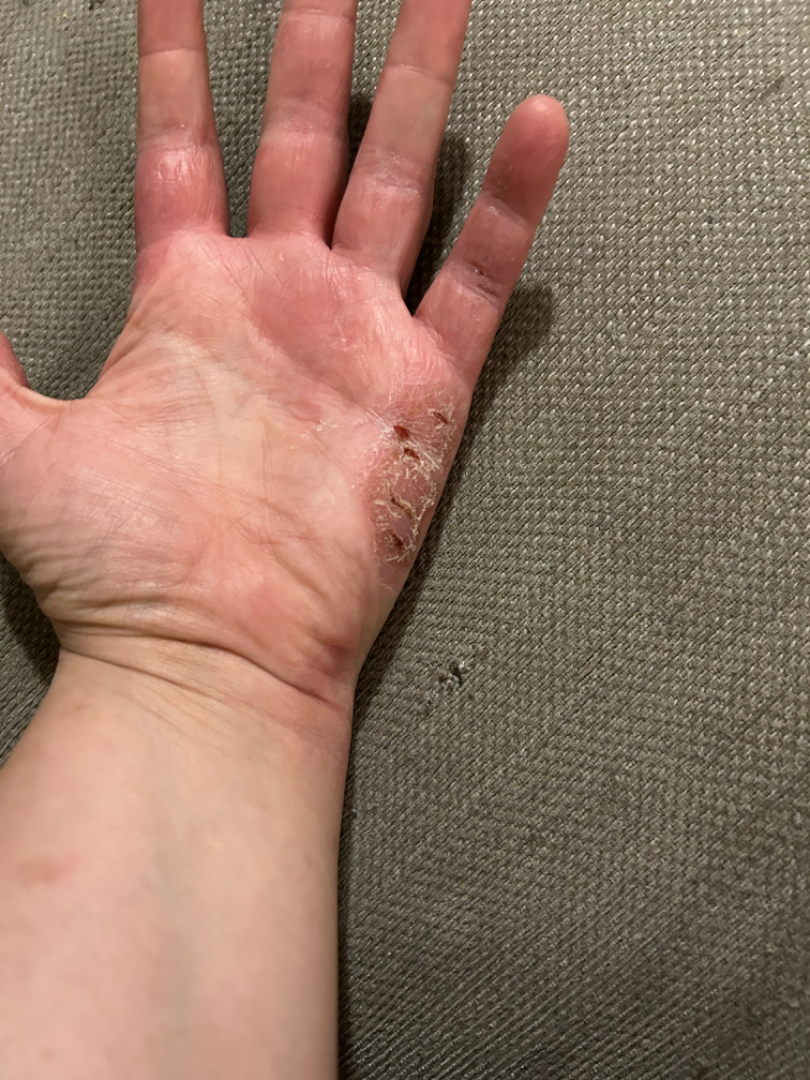An image taken at an angle.
Present for more than one year.
The patient described the issue as a rash.
The contributor reports bleeding, bothersome appearance, enlargement, darkening, pain, burning and itching.
Located on the palm.
On dermatologist assessment of the image: most consistent with Irritant Contact Dermatitis; an alternative is Psoriasis; also consider Allergic Contact Dermatitis.